A dermoscopic close-up of a skin lesion, a female subject in their mid- to late 20s — 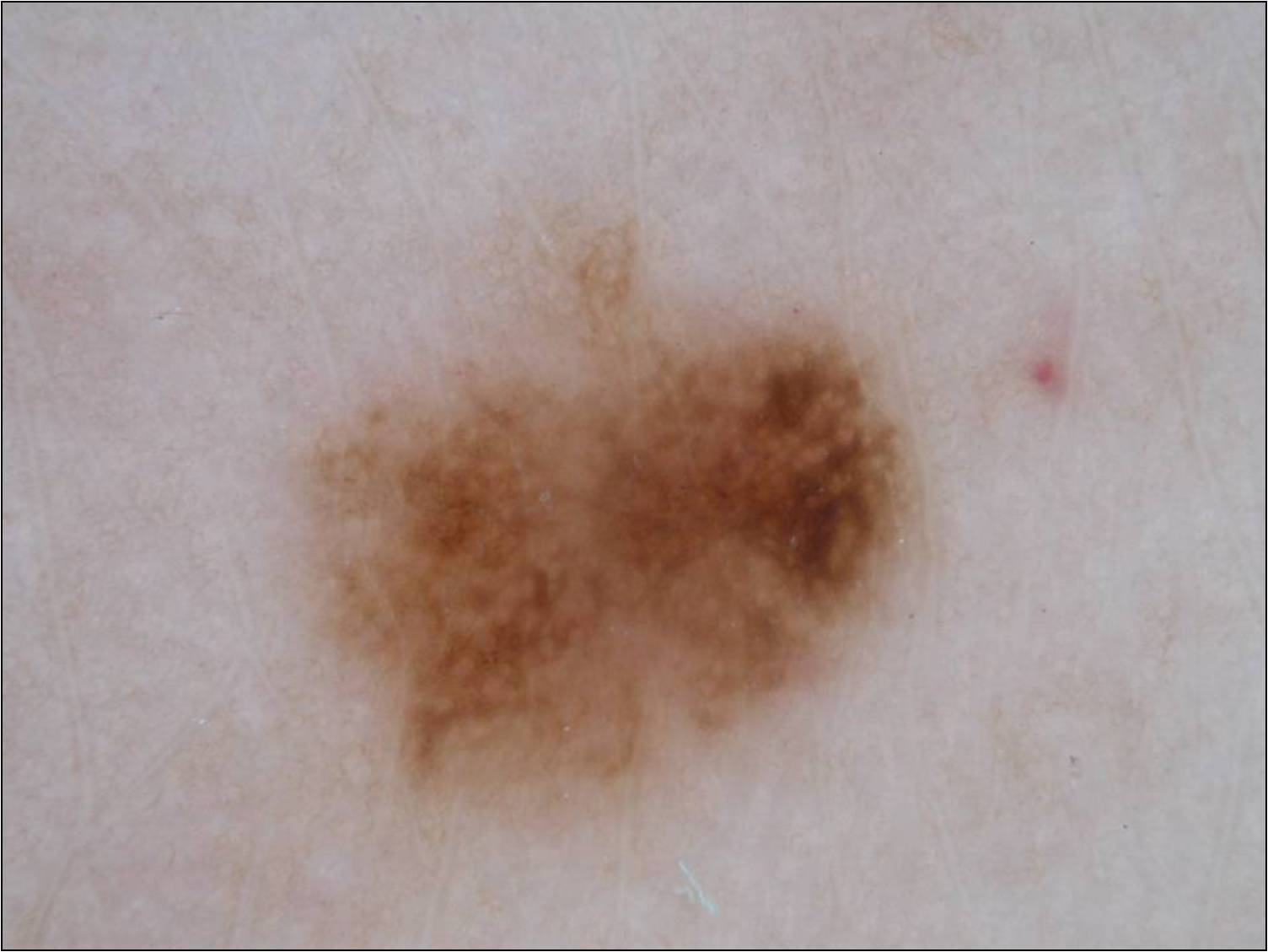dermoscopic features=pigment network; bounding box=bbox(297, 219, 927, 826); diagnosis=a melanoma, a malignancy.